The condition has been present for about one day; the lesion involves the top or side of the foot; the patient considered this a rash; this image was taken at a distance; the subject is 30–39, male; the lesion is described as fluid-filled and raised or bumpy; no relevant systemic symptoms:
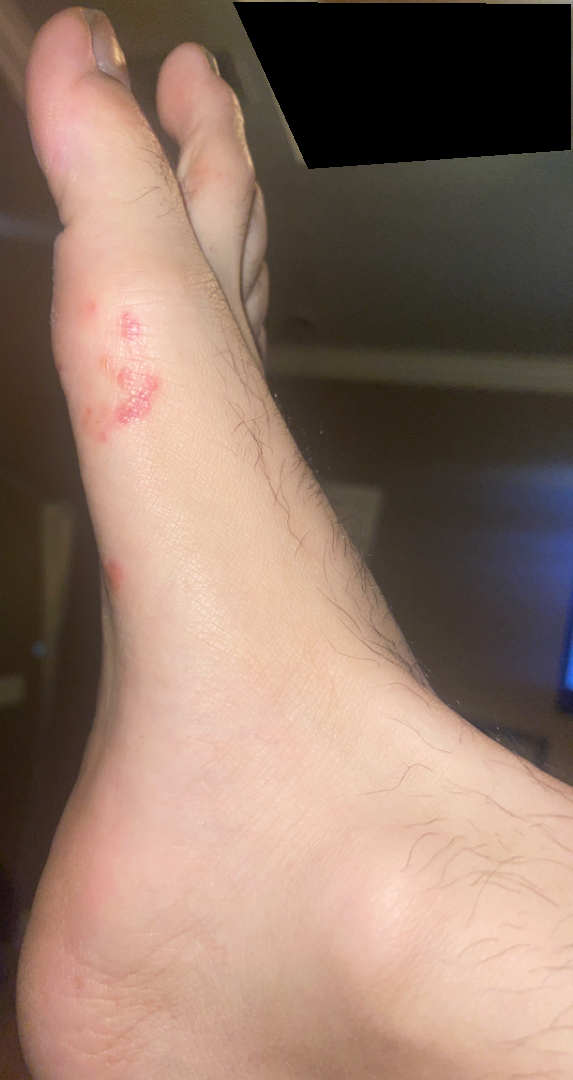differential diagnosis = three dermatologists each reviewed the case: most likely Eczema; also raised was Herpes Zoster; an alternative is Cutaneous larva migrans.